The affected area is the leg · a close-up photograph · the patient is 18–29, female.
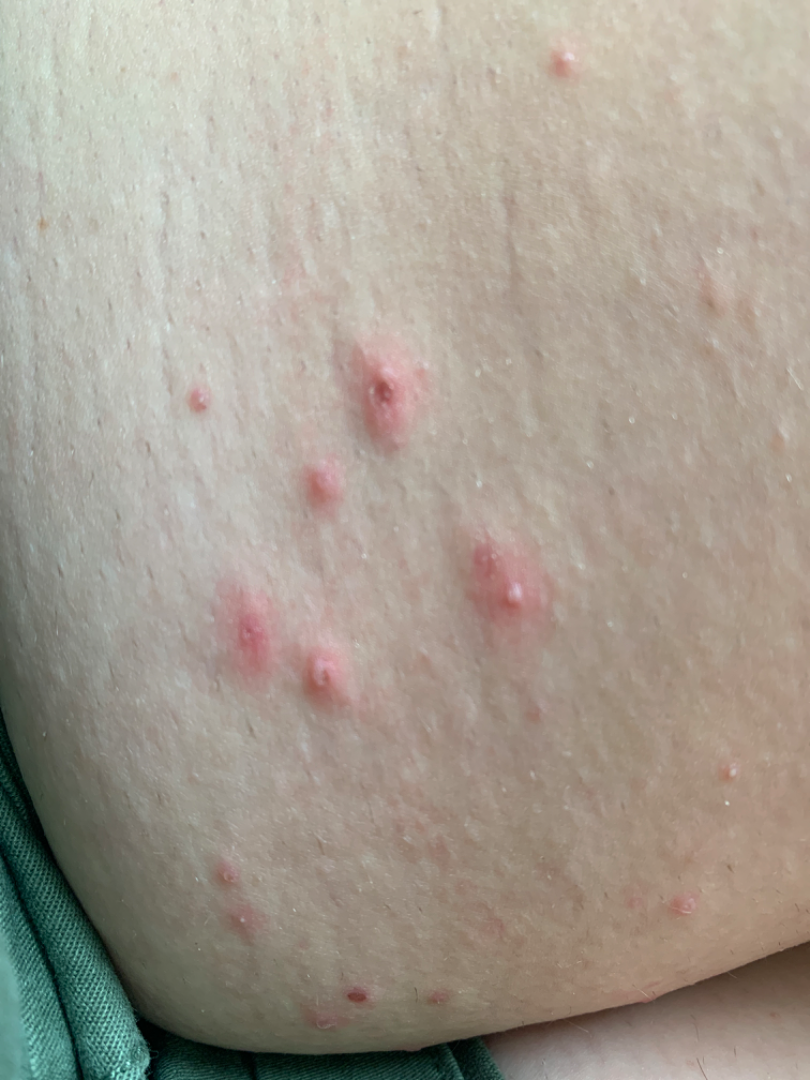On remote review of the image, the impression on review was Folliculitis.